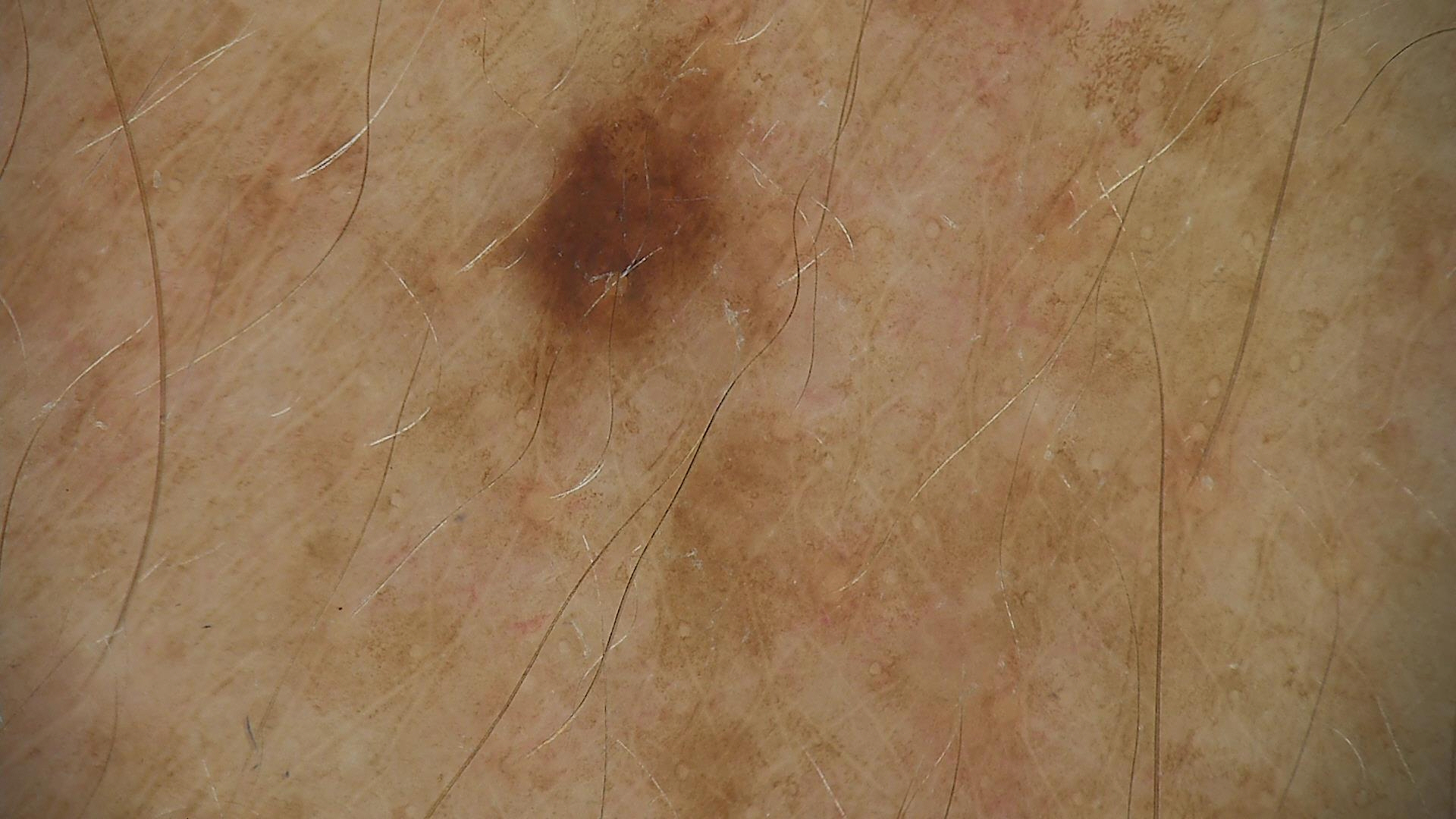A dermatoscopic image of a skin lesion. Labeled as a benign lesion — a dysplastic junctional nevus.